A dermoscopic close-up of a skin lesion: 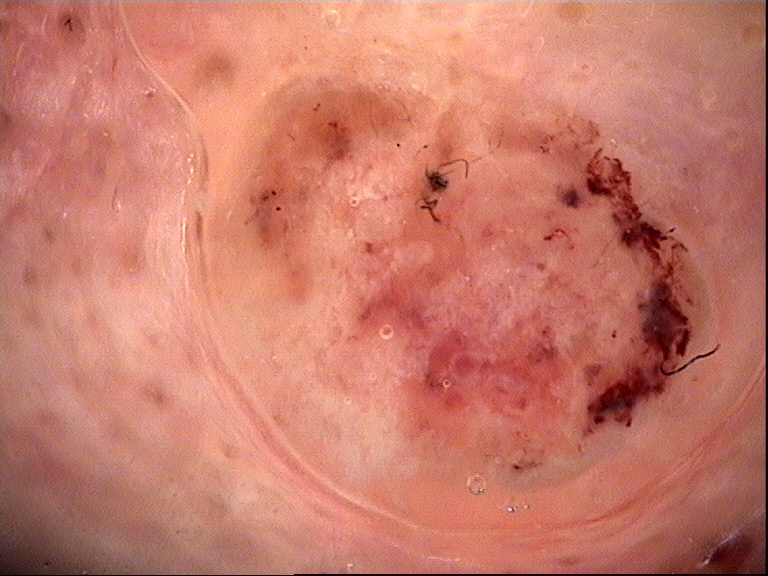Biopsy-confirmed as a keratinocytic, malignant lesion — a squamous cell carcinoma.